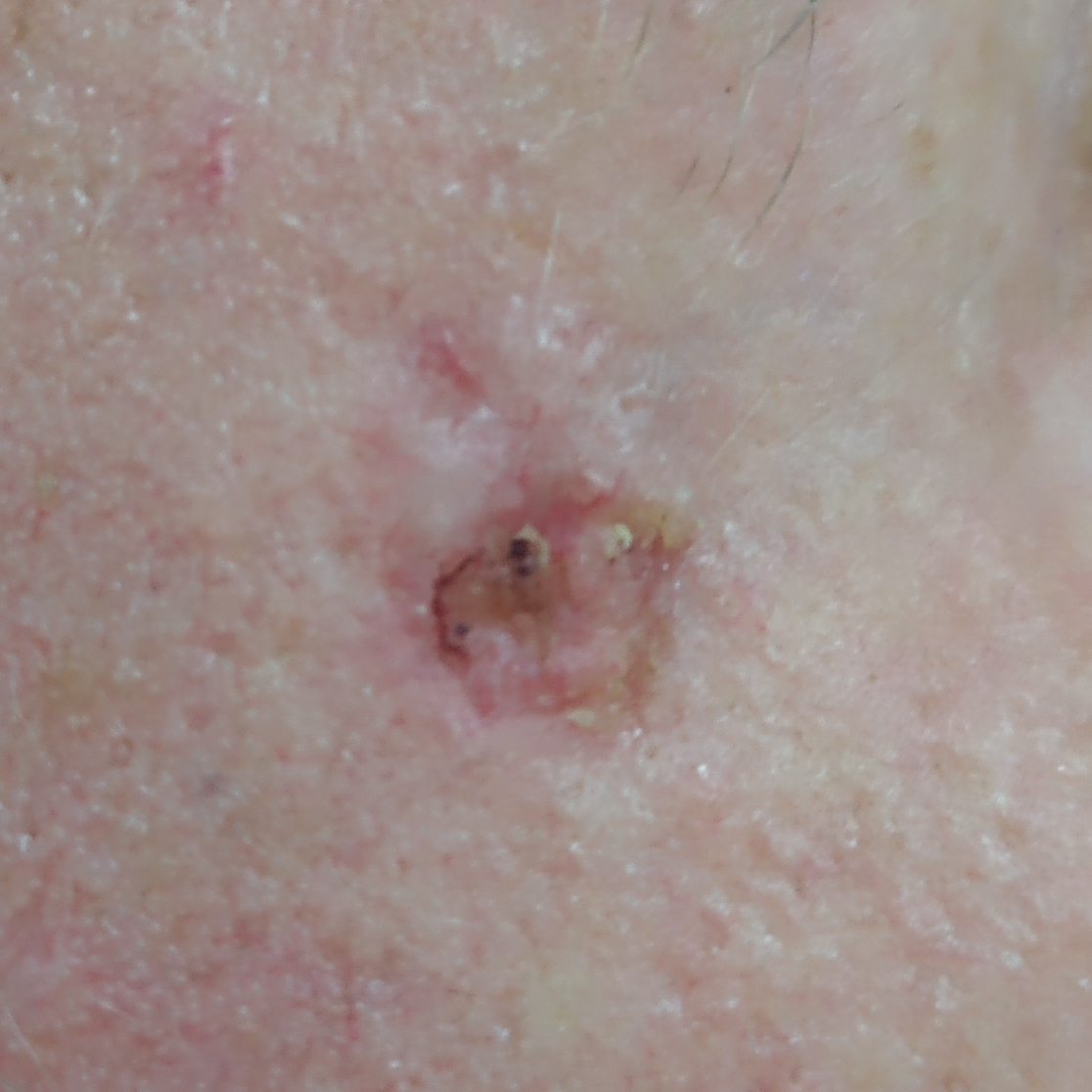A clinical photo of a skin lesion taken with a smartphone. A male patient 31 years old. The chart notes alcohol use and pesticide exposure. The lesion is on the face. Measuring about 10 × 7 mm. The patient describes that the lesion has bled, has grown, and is elevated, but does not itch and has not changed. The biopsy diagnosis was a basal cell carcinoma.